The patient is 40–49, female. The back of the hand is involved. The photo was captured at an angle.
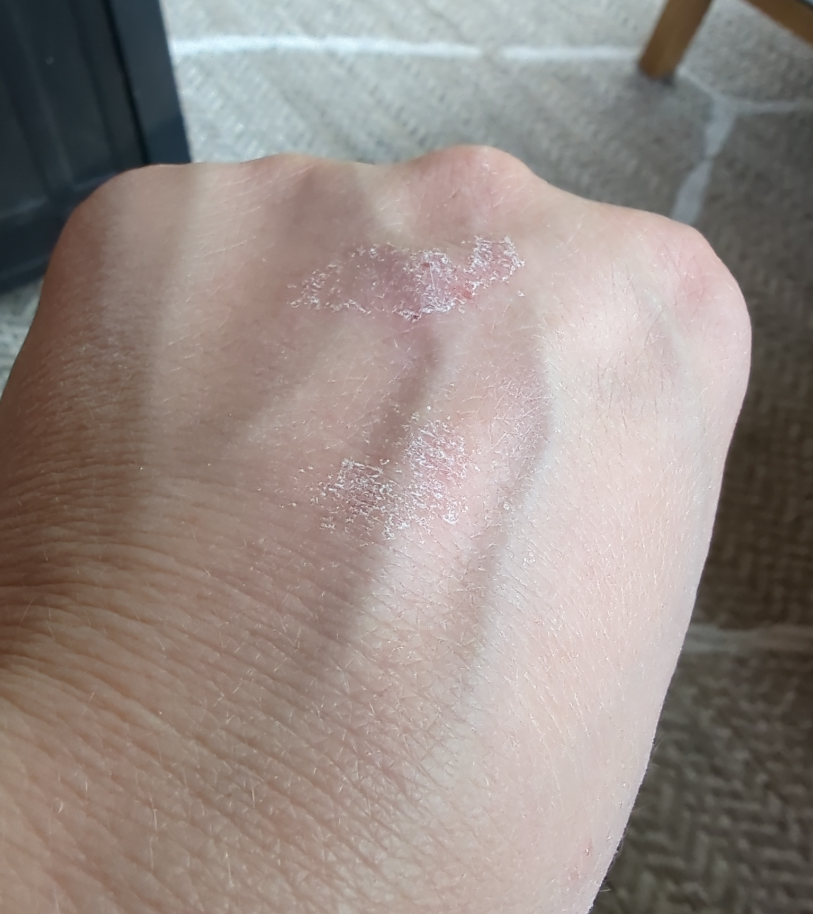The differential is split between Psoriasis and Eczema.